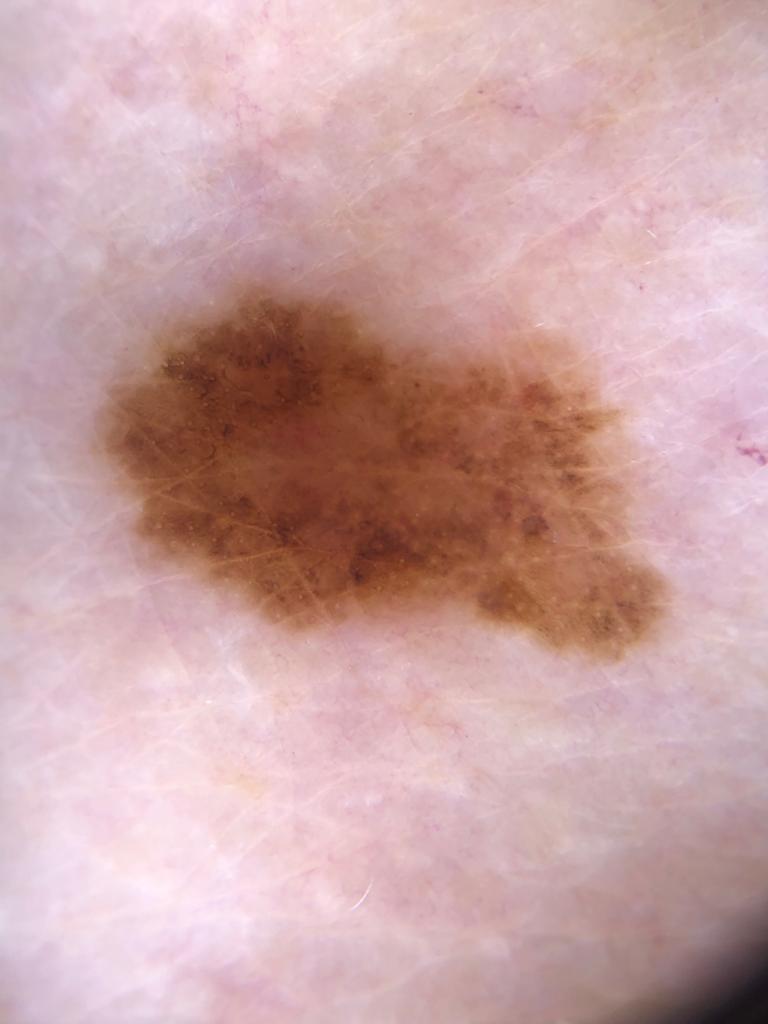image: dermoscopic image
patient:
  age_approx: 75
  sex: female
lesion_location:
  region: an upper extremity
diagnosis:
  name: Melanoma
  malignancy: malignant
  confirmation: histopathology